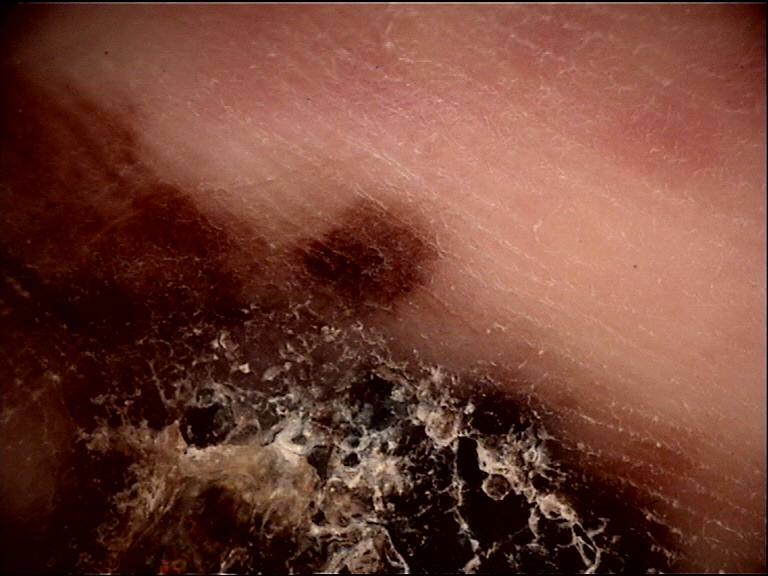Summary:
A dermoscopic image of a skin lesion.
Diagnosis:
Histopathology confirmed a skin cancer — an acral lentiginous melanoma.